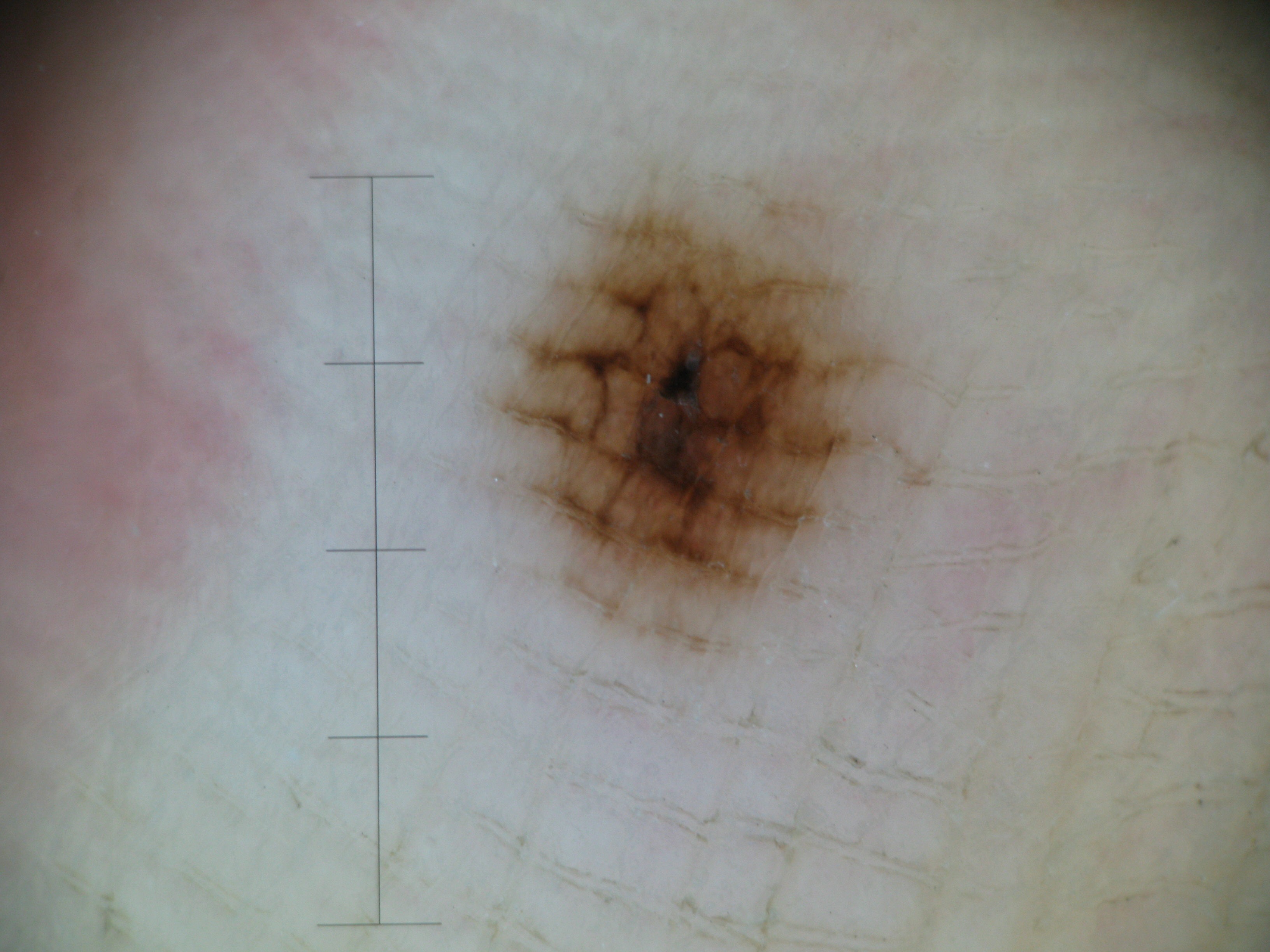Q: What is the diagnosis?
A: acral junctional nevus (expert consensus)